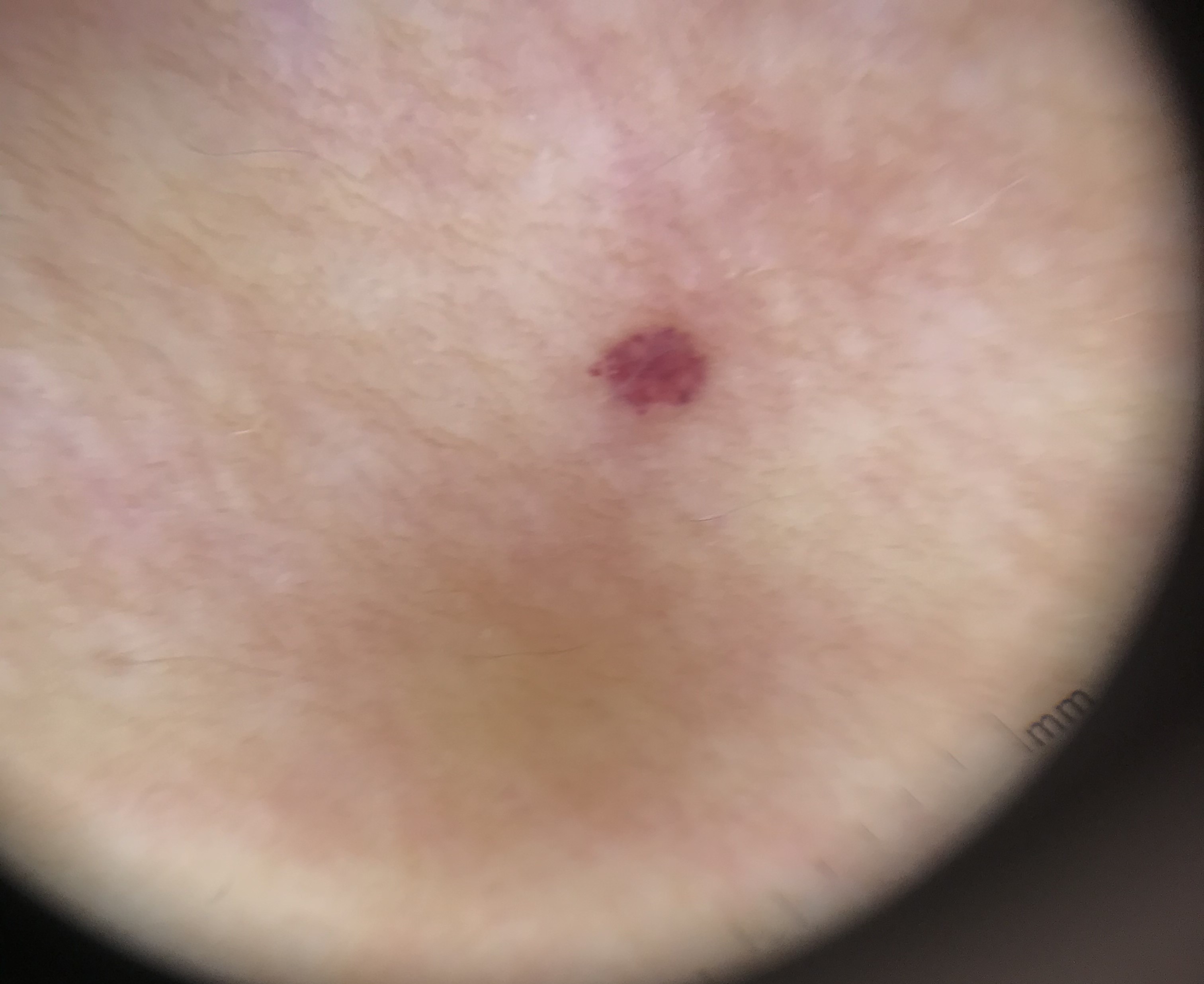Classified as a hemangioma.